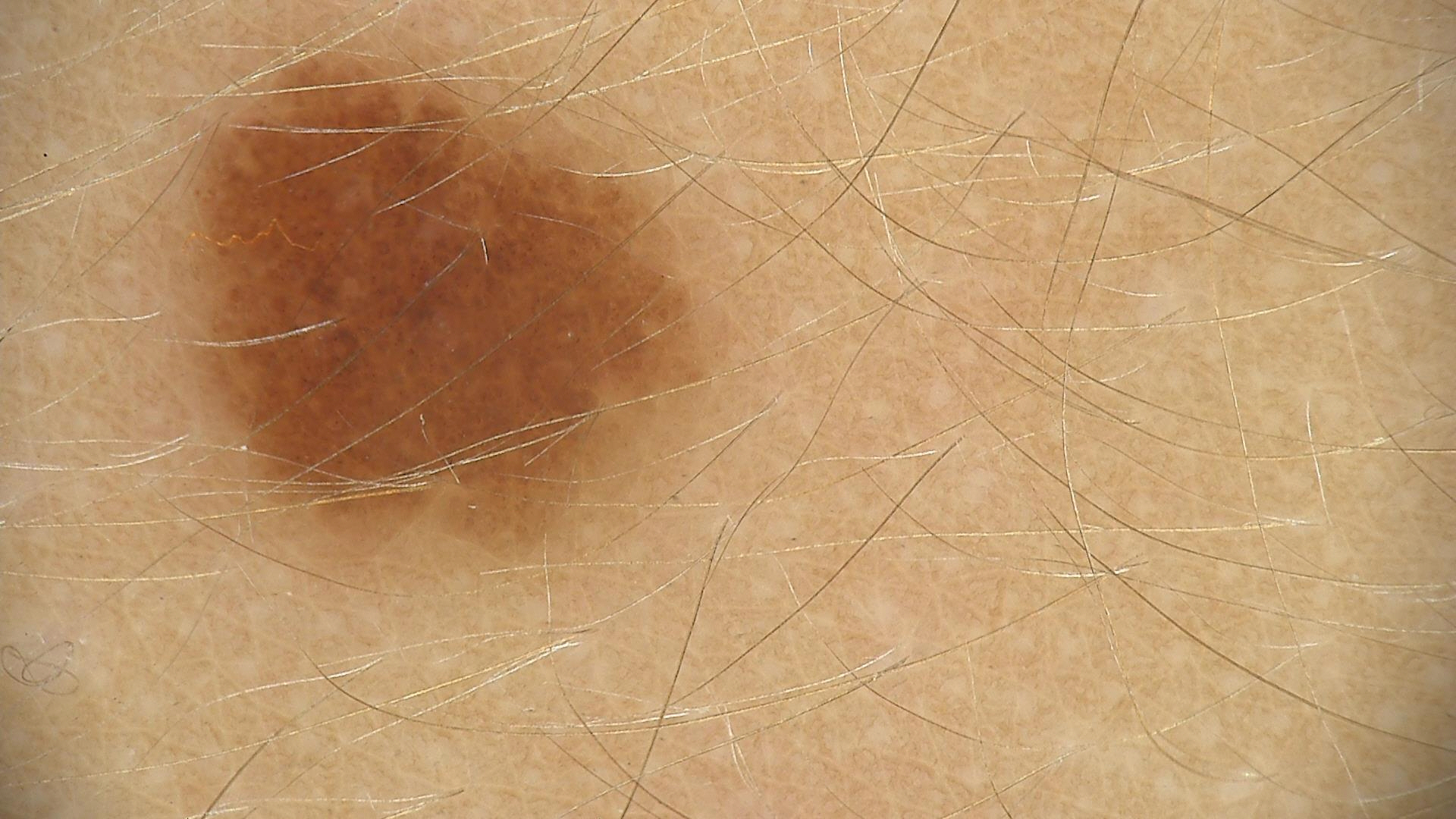modality = dermatoscopy; diagnostic label = junctional nevus (expert consensus).